On a questionnaire the patient reported a personal history of cancer, a family history of skin cancer, and no prior organ transplant; a female patient aged 64; the patient says their skin tans without first burning; referred for assessment of suspected melanocytic nevus; a skin lesion imaged with a dermatoscope:
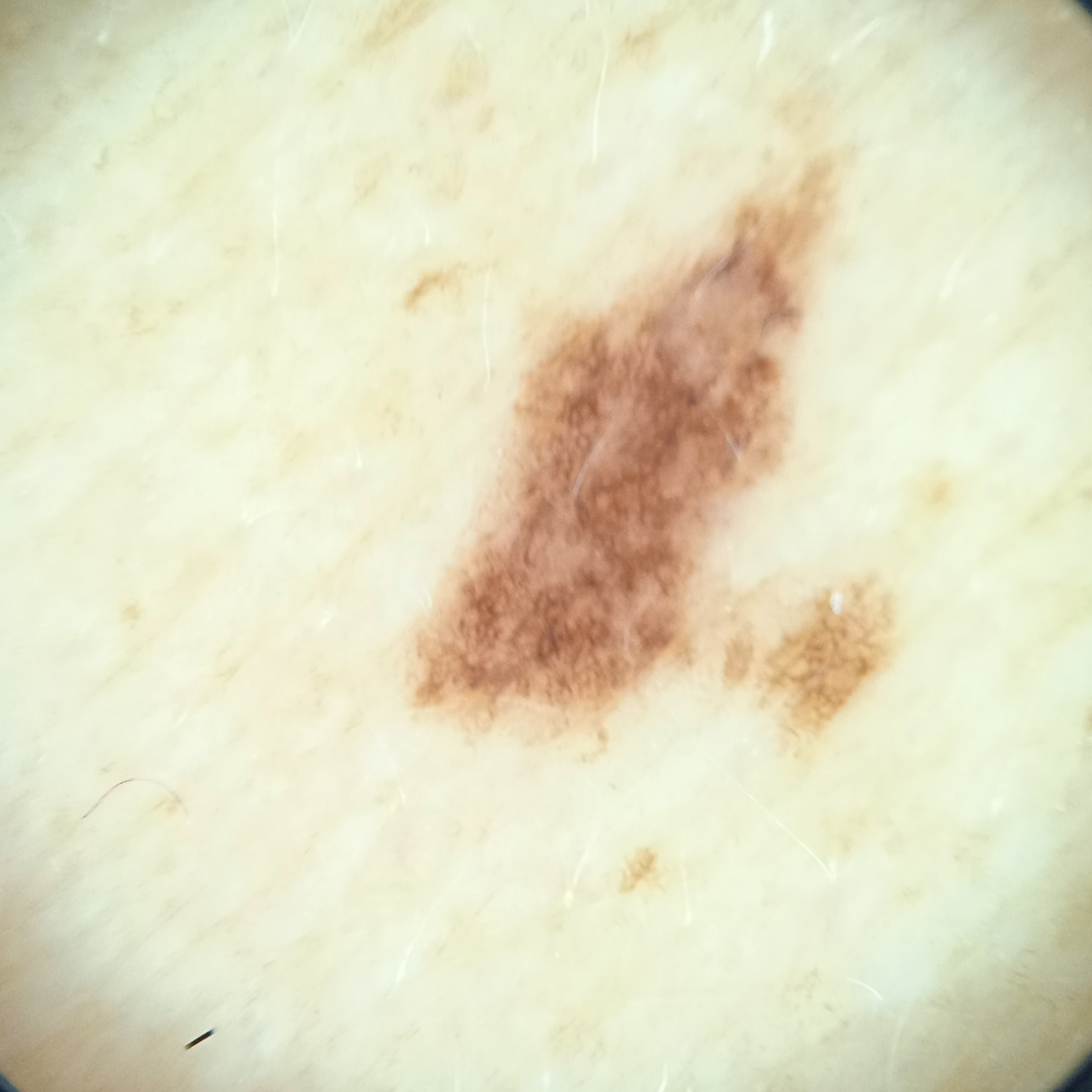The lesion is on the back. The lesion is about 8.3 mm across. The biopsy diagnosis was an atypical (dysplastic) nevus, following excision.